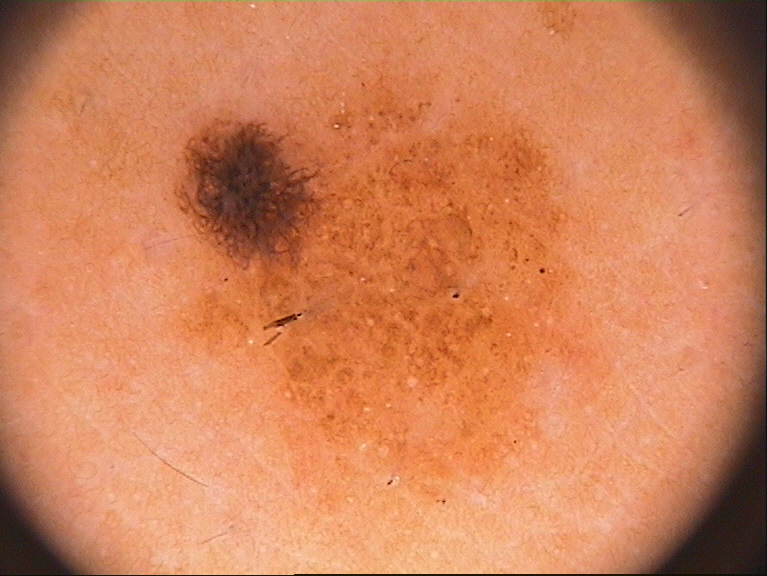Findings: A dermoscopic view of a skin lesion. A male patient aged 23-27. The lesion occupies the region 161 35 599 509. A large lesion occupying much of the field. Dermoscopic examination shows globules and pigment network; no streaks, milia-like cysts, or negative network. Impression: Clinically diagnosed as a melanocytic nevus.